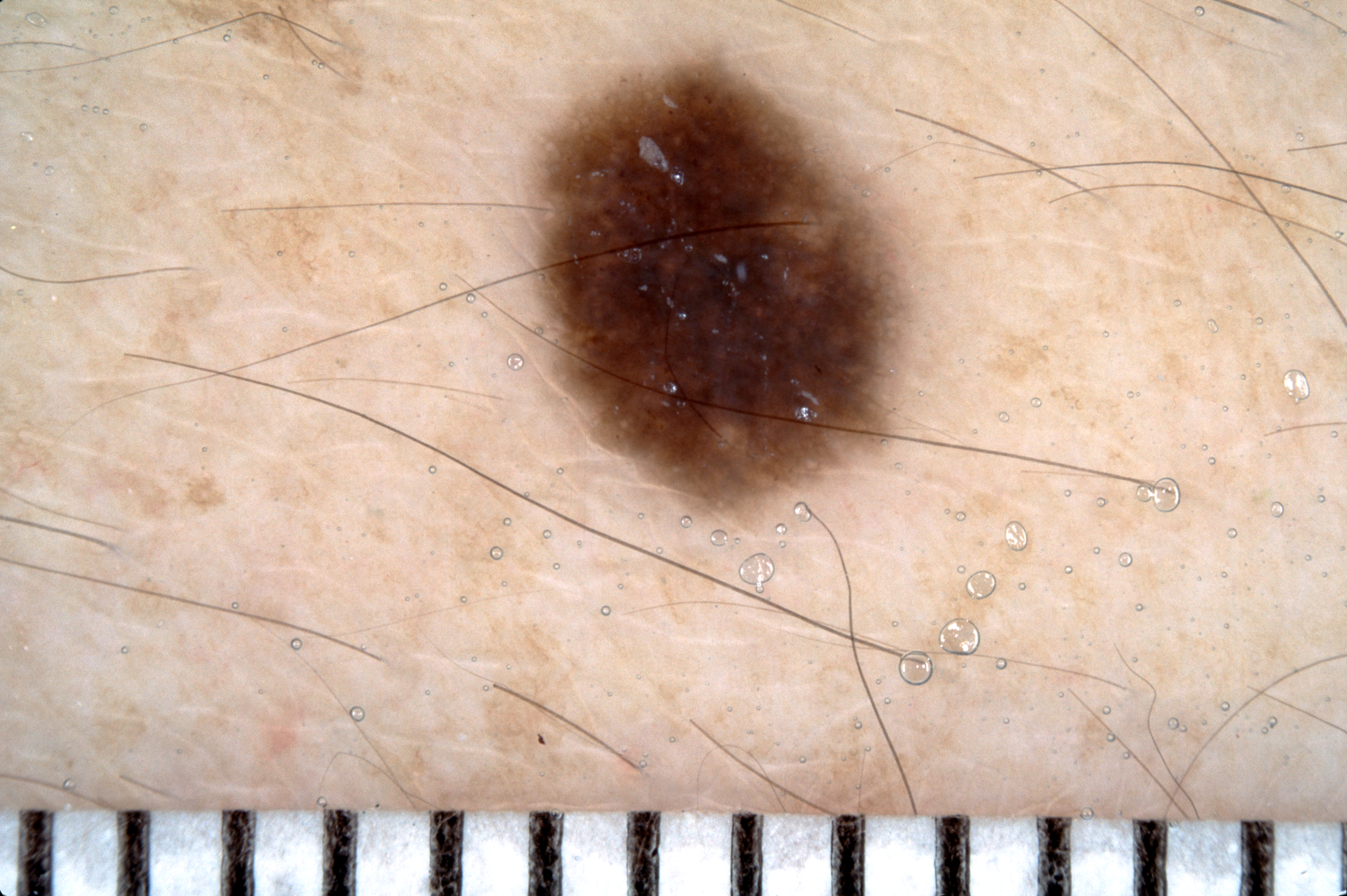Image and clinical context:
A female subject, approximately 35 years of age. A dermoscopy image of a single skin lesion. In (x1, y1, x2, y2) order, the lesion occupies the region [547, 63, 905, 511]. The dermoscopic pattern shows pigment network. A moderately sized lesion.
Conclusion:
The lesion was assessed as a melanocytic nevus, a benign lesion.